A dermoscopy image of a single skin lesion:
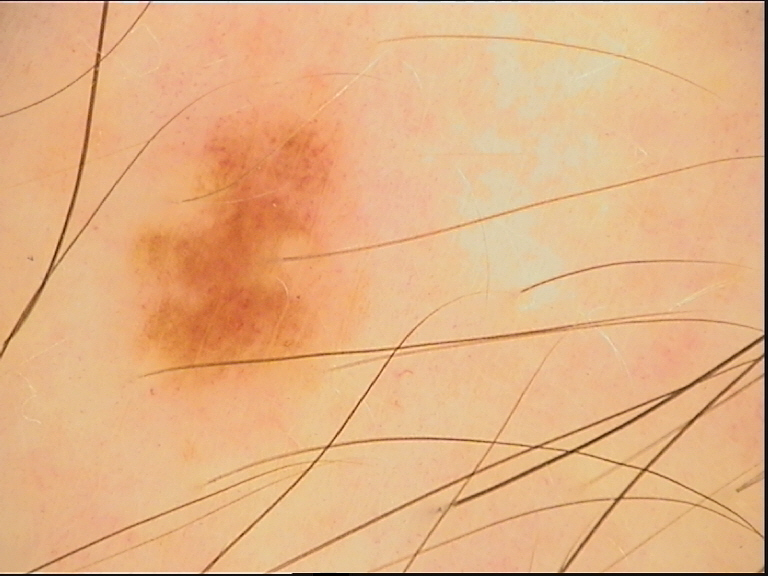Conclusion:
Consistent with a benign lesion — a dysplastic junctional nevus.